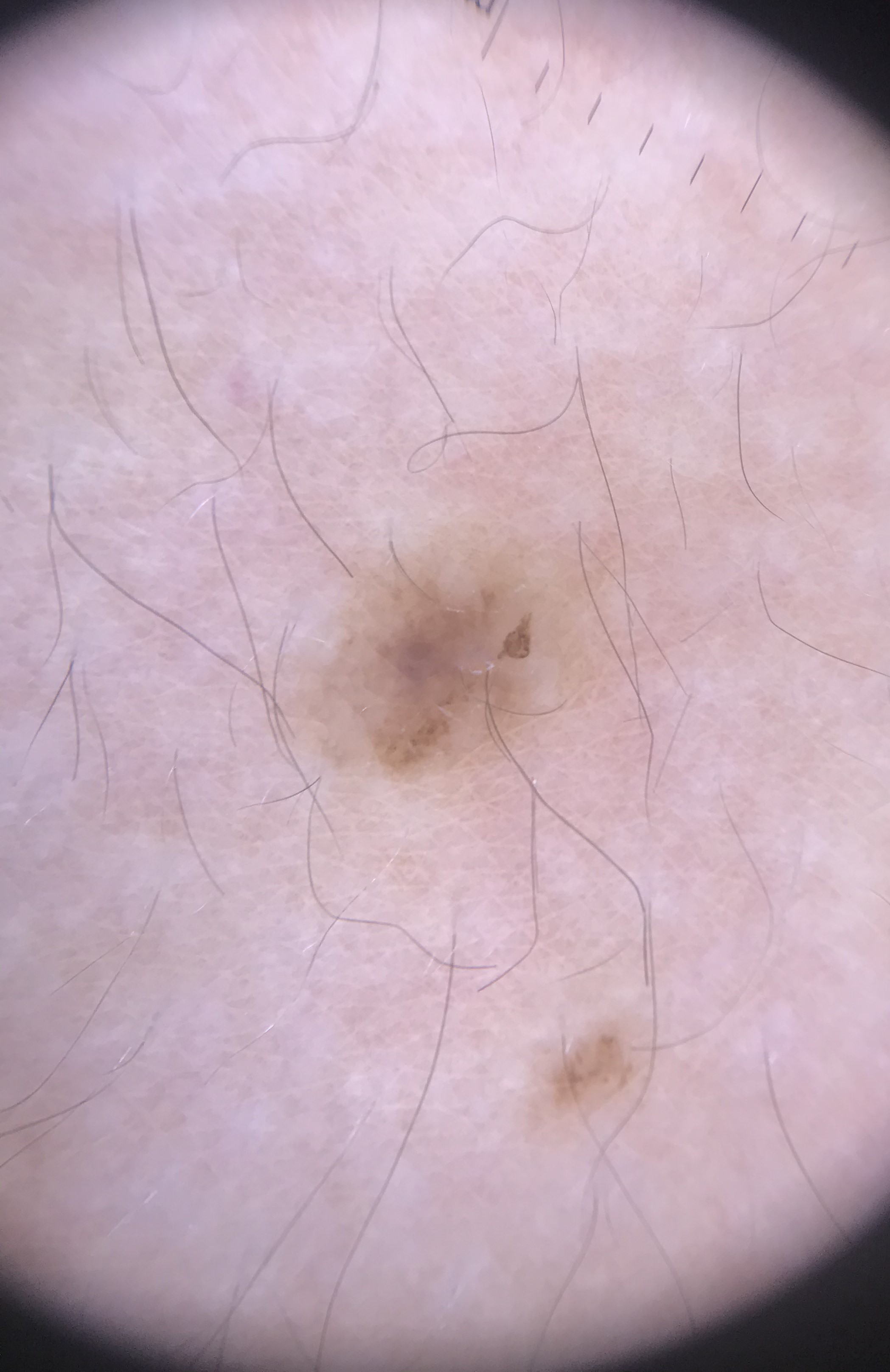Labeled as a banal lesion — a compound nevus.